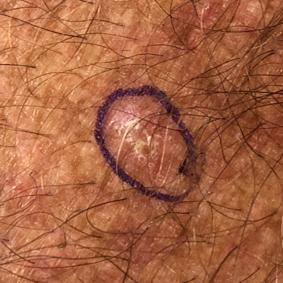Clinical context: The patient was assessed as Fitzpatrick skin type III. A male subject aged 55. The chart records prior skin cancer (patient or family), pesticide exposure, alcohol use, and prior malignancy (patient or family). A clinical close-up photograph of a skin lesion. The lesion involves a forearm. The lesion measures approximately 6 × 5 mm. Conclusion: The clinical impression was a lesion with uncertain malignant potential — an actinic keratosis.